A female patient aged around 45. A wide-field clinical photograph of a skin lesion — 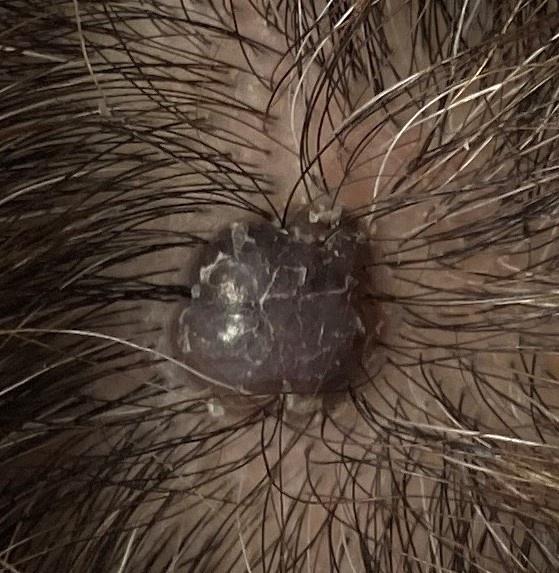{
  "lesion_location": {
    "region": "the head or neck"
  },
  "diagnosis": {
    "name": "Basal cell carcinoma",
    "malignancy": "malignant",
    "confirmation": "histopathology",
    "lineage": "adnexal"
  }
}